A skin lesion imaged with a dermatoscope.
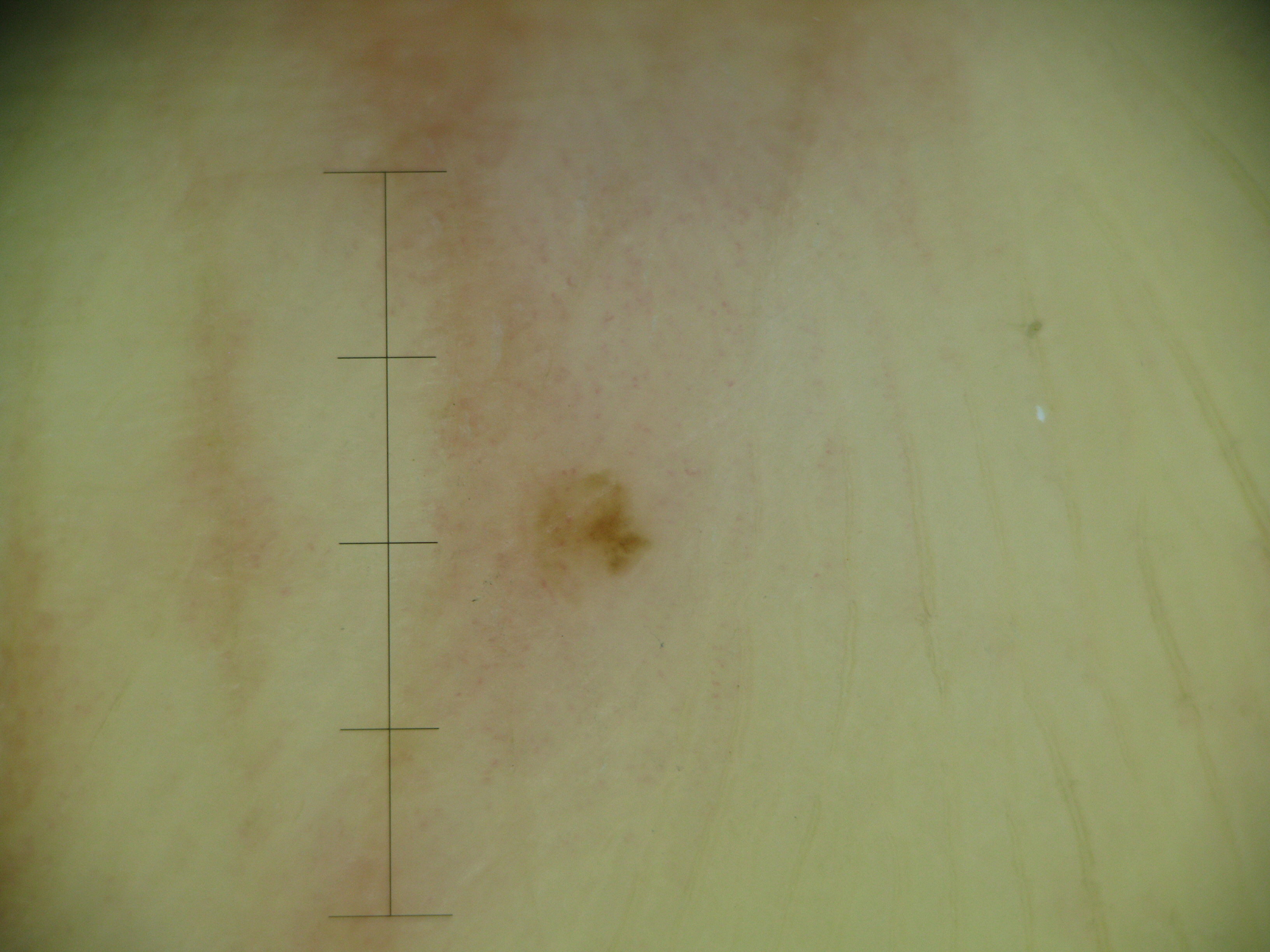Conclusion:
Labeled as a banal lesion — an acral junctional nevus.